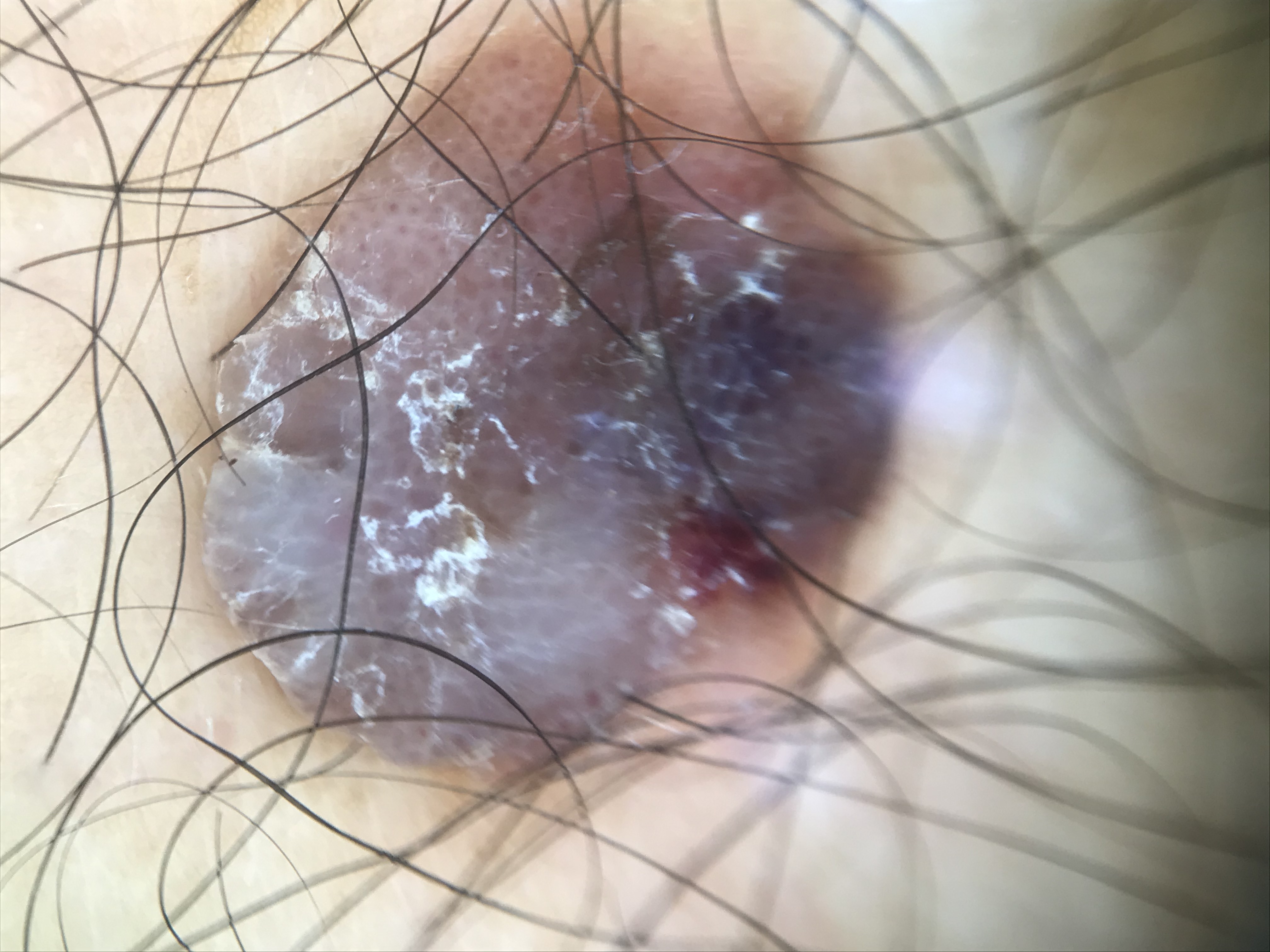Labeled as a seborrheic keratosis.